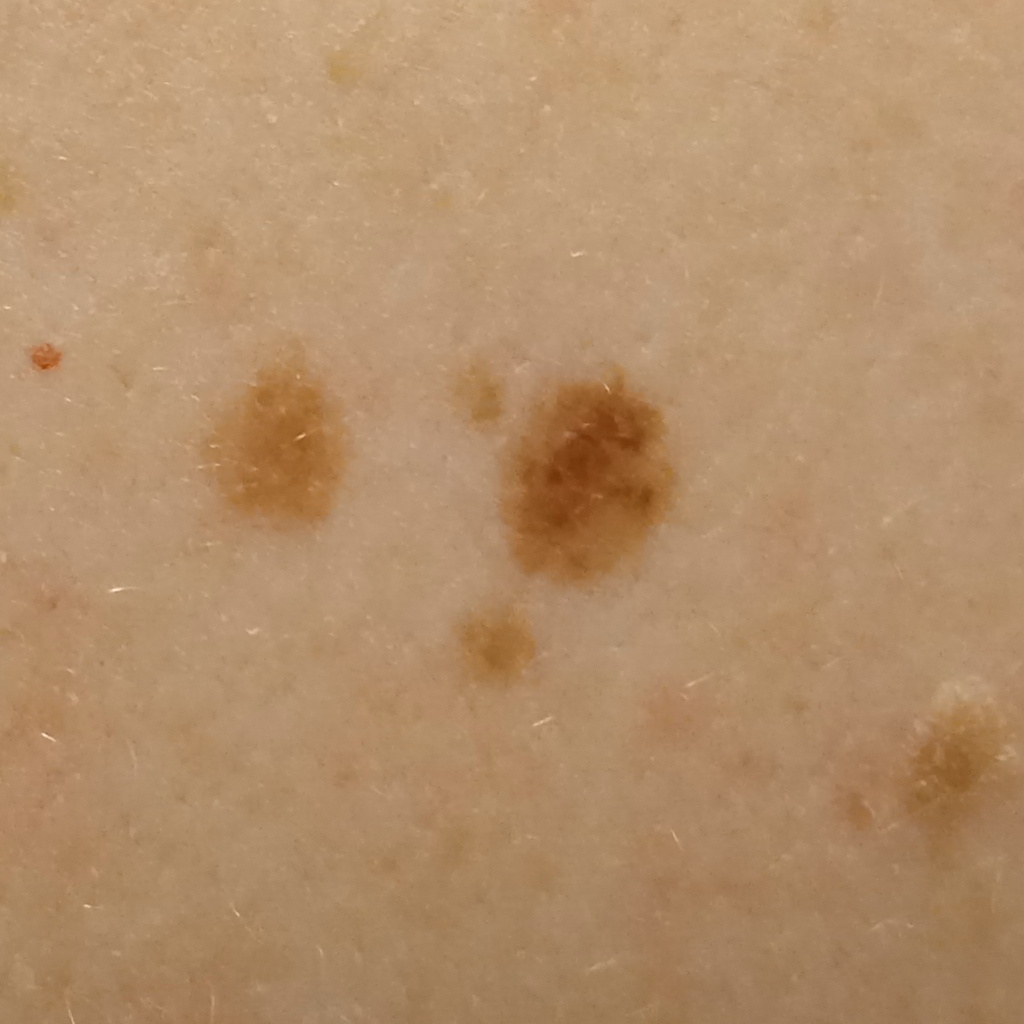A female patient 54 years old. A clinical photograph showing a skin lesion. Numerous moles by the patient's own estimate. The patient says their skin reddens with sun exposure. On a questionnaire the patient reported a family history of skin cancer, a personal history of skin cancer, and a personal history of cancer. Acquired for a research image collection, with no referral diagnosis. The lesion is on the back. The lesion is about 6.4 mm across. The consensus diagnosis for this lesion was an atypical (dysplastic) nevus.